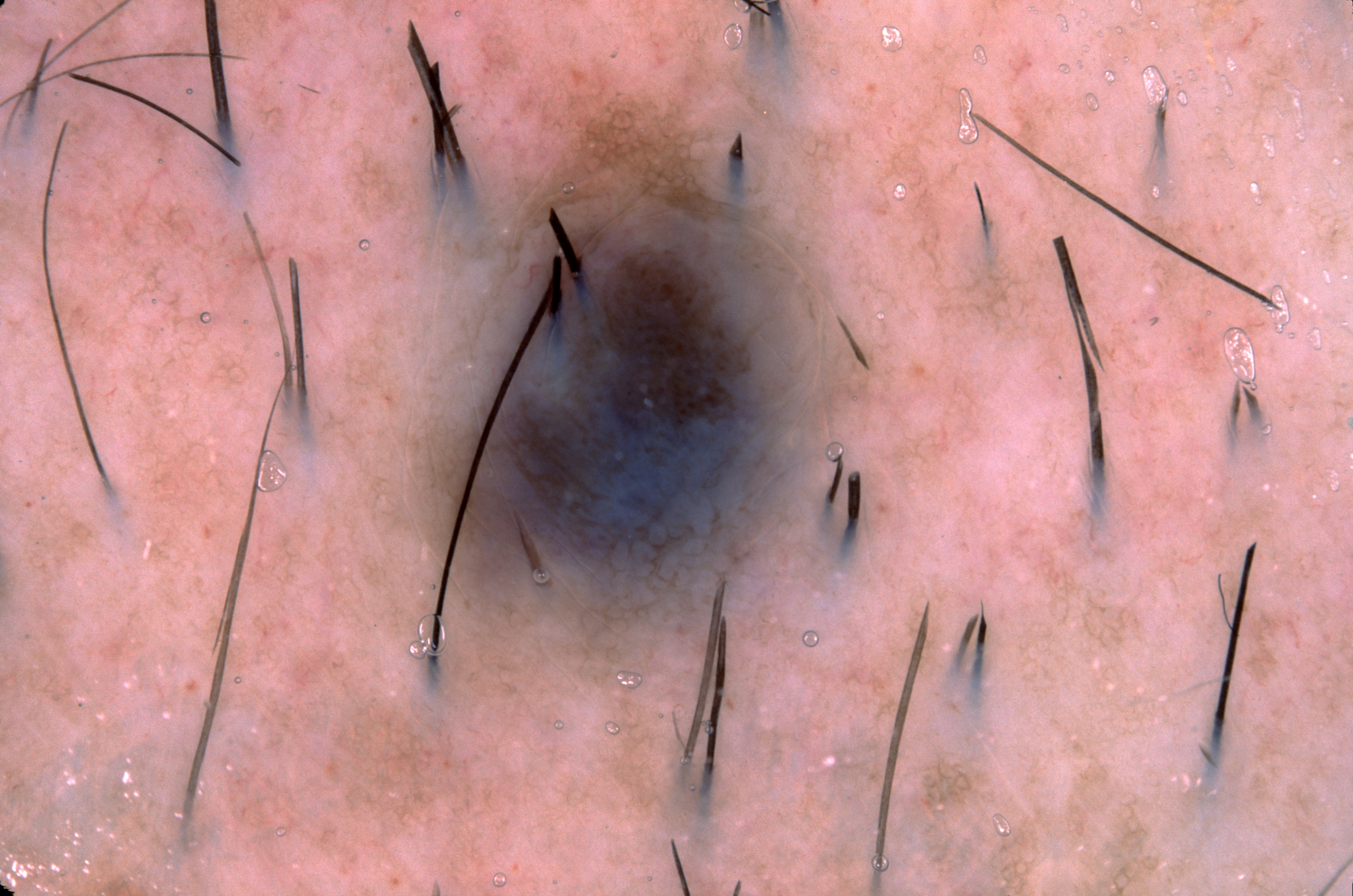The patient is a male aged 53-57. A dermoscopic image of a skin lesion. A mid-sized lesion within the field. The lesion's extent is left=374, top=129, right=852, bottom=672. Dermoscopic review identifies pigment network, with no negative network, milia-like cysts, or streaks. The clinical diagnosis was a melanocytic nevus, a benign skin lesion.